The lesion is described as rough or flaky and raised or bumpy, self-categorized by the patient as a rash, this is a close-up image, located on the top or side of the foot, no relevant systemic symptoms:
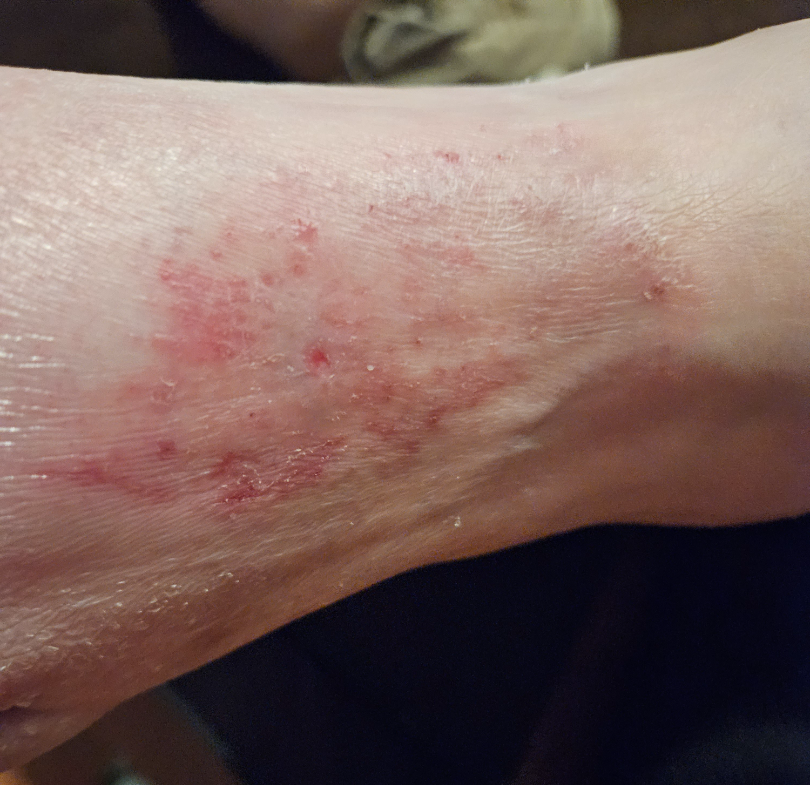clinical impression: the leading consideration is Tinea; the differential also includes Eczema; also raised was Allergic Contact Dermatitis.